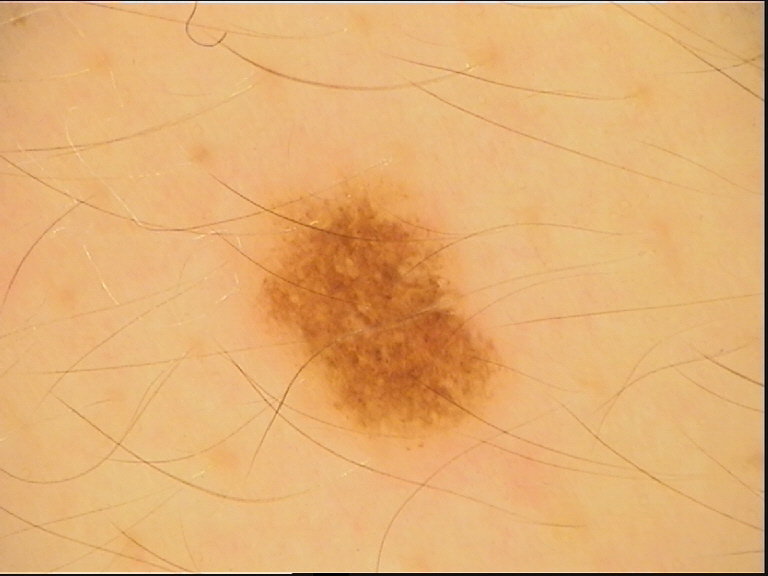Findings:
• image type — dermoscopy
• class — dysplastic junctional nevus (expert consensus)